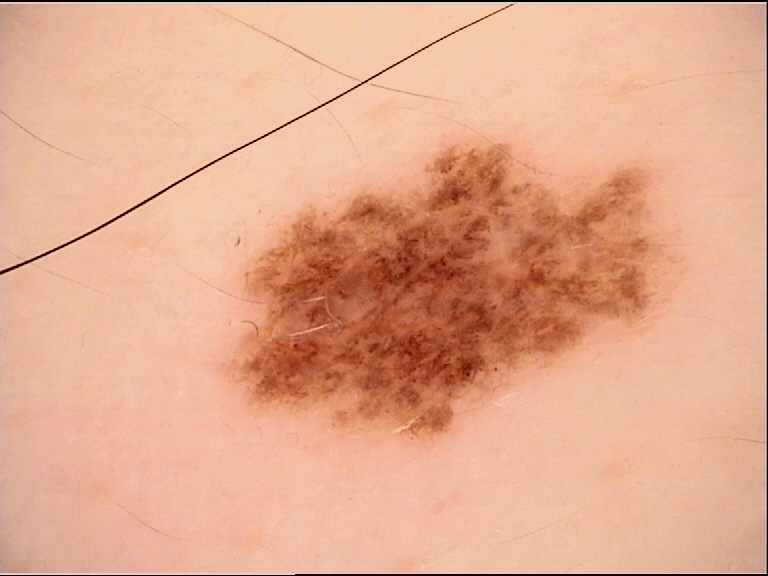{
  "diagnosis": {
    "name": "dysplastic junctional nevus",
    "code": "jd",
    "malignancy": "benign",
    "super_class": "melanocytic",
    "confirmation": "expert consensus"
  }
}